Self-categorized by the patient as a rash. Reported duration is one to four weeks. The photograph is a close-up of the affected area. The subject is 18–29, female. The lesion is described as fluid-filled, raised or bumpy and rough or flaky. The patient indicates associated fatigue, fever, joint pain and mouth sores. Located on the arm. Skin tone: Fitzpatrick skin type I; lay graders estimated 2 on the Monk skin tone scale: 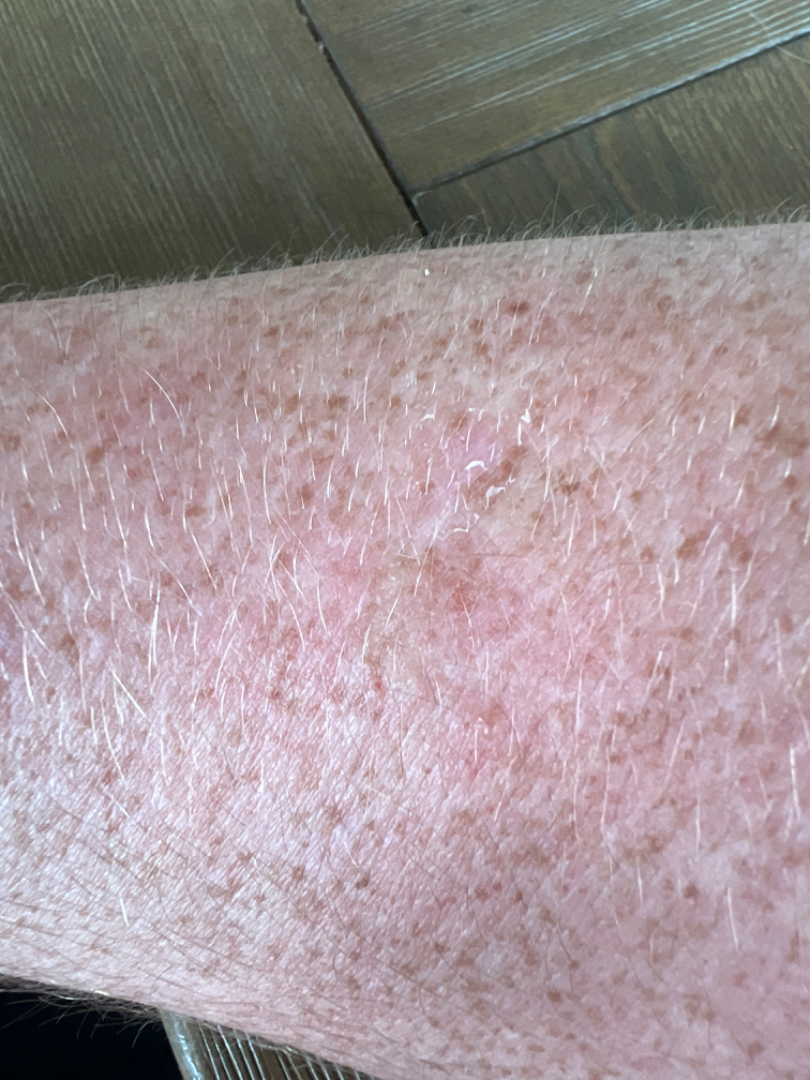<case>
  <differential>
    <tied_lead>Eczema, Photodermatitis, Allergic Contact Dermatitis, Lentigo, Sunburn, Acquired poikiloderma</tied_lead>
  </differential>
</case>